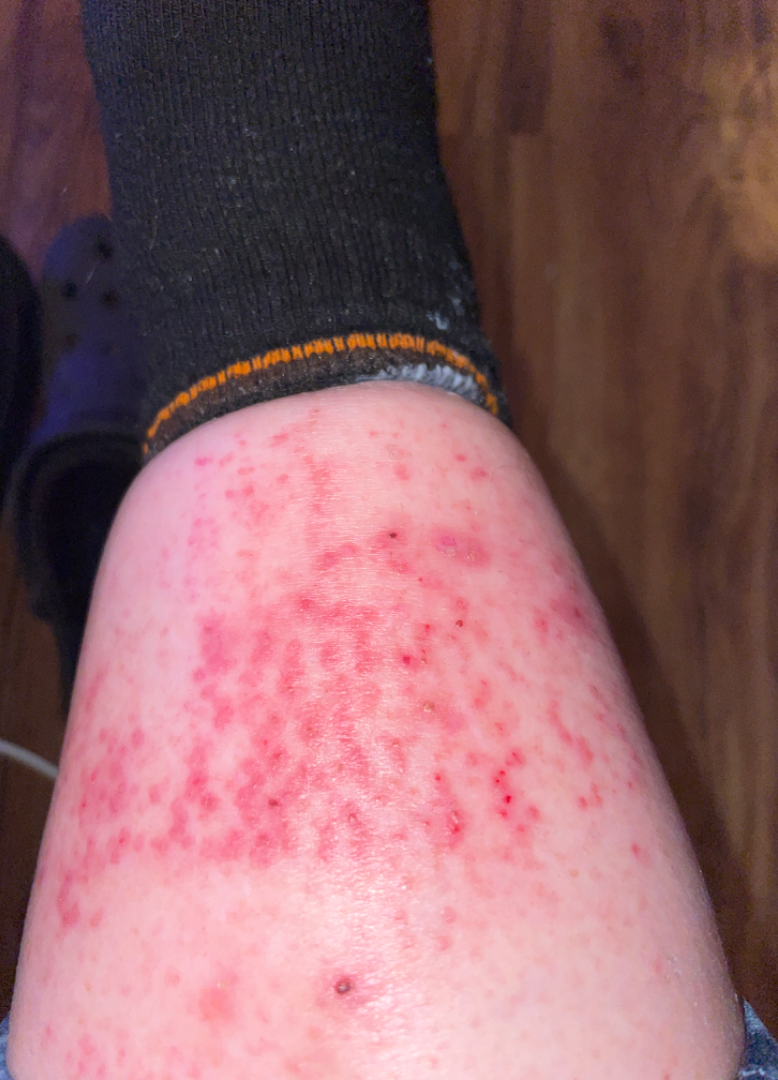Q: Patient demographics?
A: female, age 50–59
Q: Patient's own categorization?
A: a rash
Q: What is the framing?
A: close-up
Q: Reported symptoms?
A: enlargement and itching
Q: When did this start?
A: less than one week
Q: Anatomic location?
A: leg
Q: Texture?
A: flat and raised or bumpy
Q: What conditions are considered?
A: the primary impression is Eczema; also consider Irritant Contact Dermatitis; a remote consideration is Folliculitis; less probable is Xerosis; less likely is Stasis Dermatitis; lower on the differential is Leukocytoclastic Vasculitis